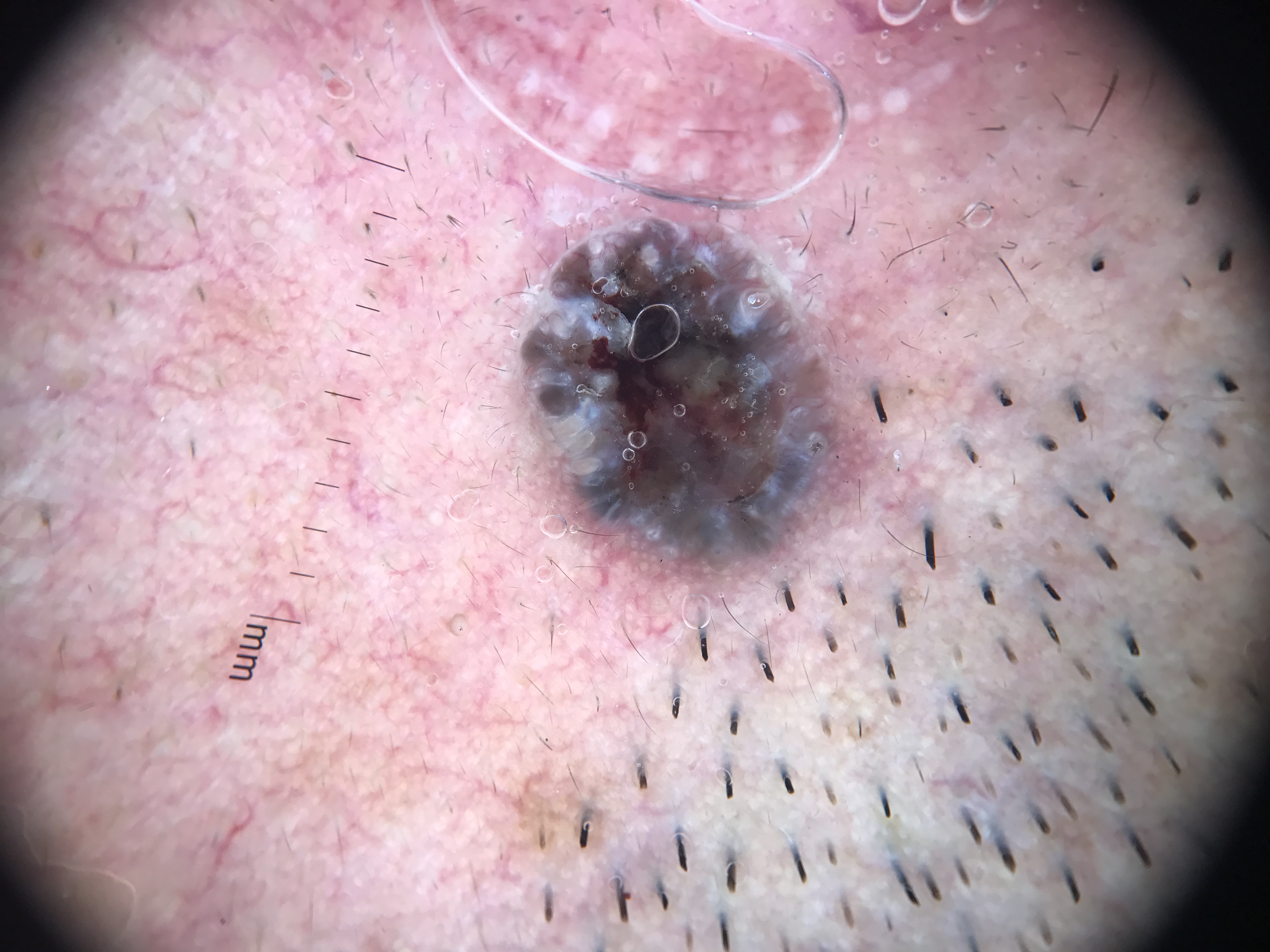Findings: A dermoscopic image of a skin lesion. Conclusion: Histopathologically confirmed as a keratinocytic, malignant lesion — a basal cell carcinoma.